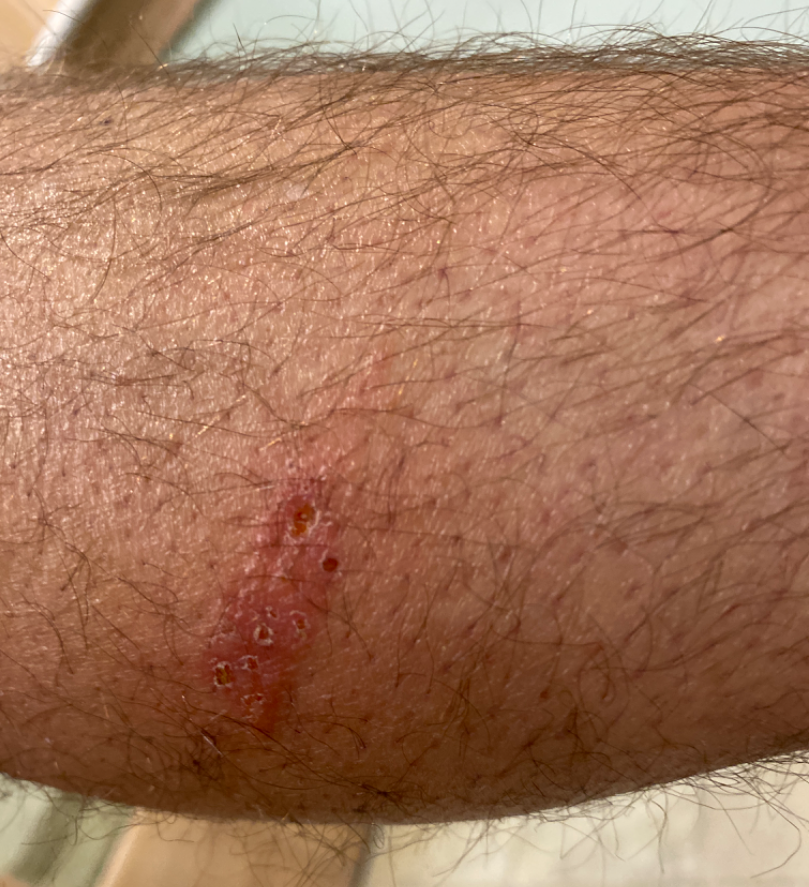{"assessment": "could not be assessed", "systemic_symptoms": "none reported", "patient_category": "a rash", "texture": "raised or bumpy", "symptoms": "itching", "shot_type": "at an angle", "body_site": ["leg", "arm"]}